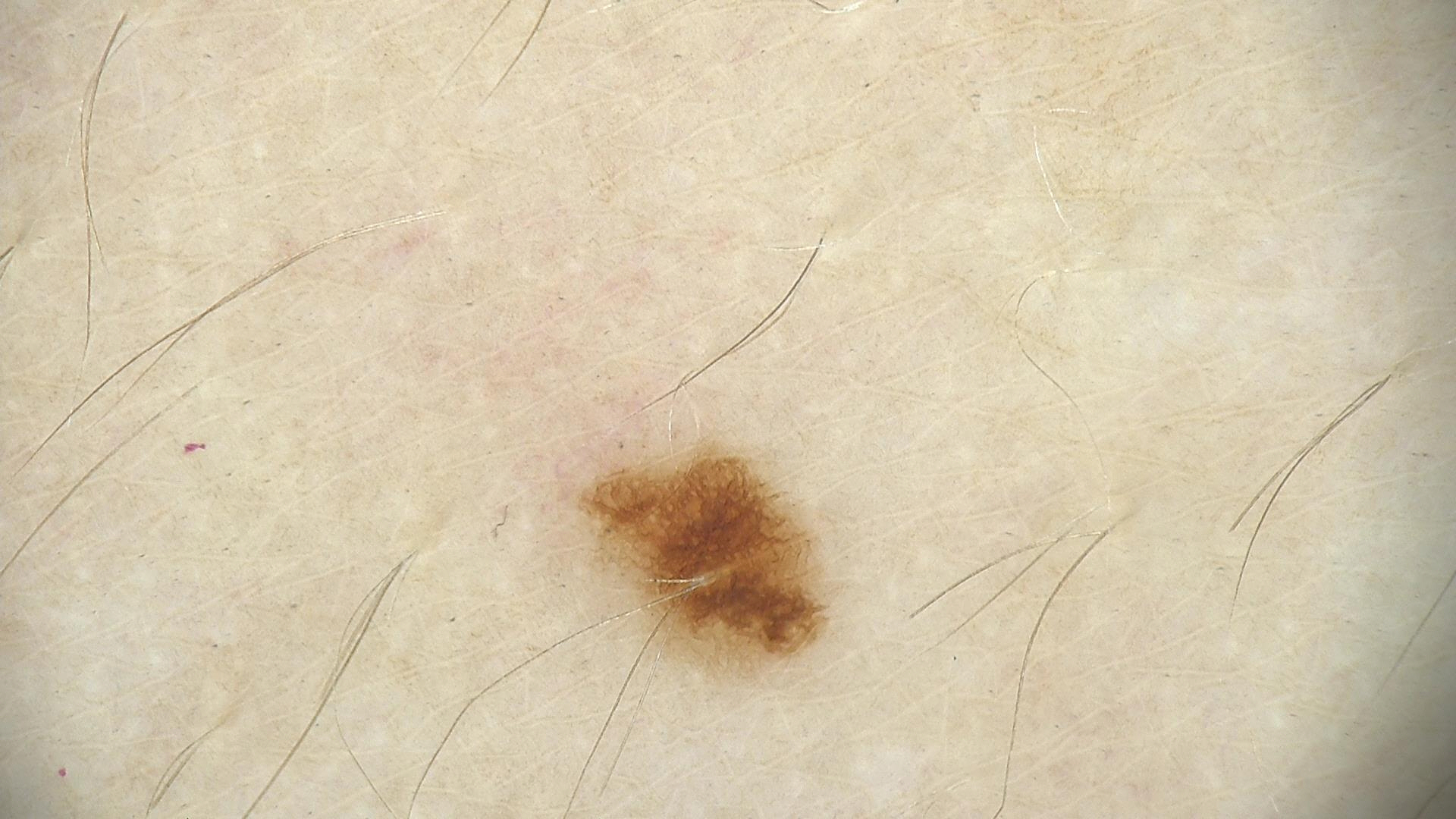imaging — dermoscopy; diagnostic label — dysplastic junctional nevus (expert consensus).